The front of the torso and head or neck are involved; close-up view; non-clinician graders estimated 2 on the Monk skin tone scale; symptoms reported: itching; no relevant systemic symptoms; the subject is 50–59, female; the contributor notes the lesion is raised or bumpy; self-categorized by the patient as a rash; present for about one day — 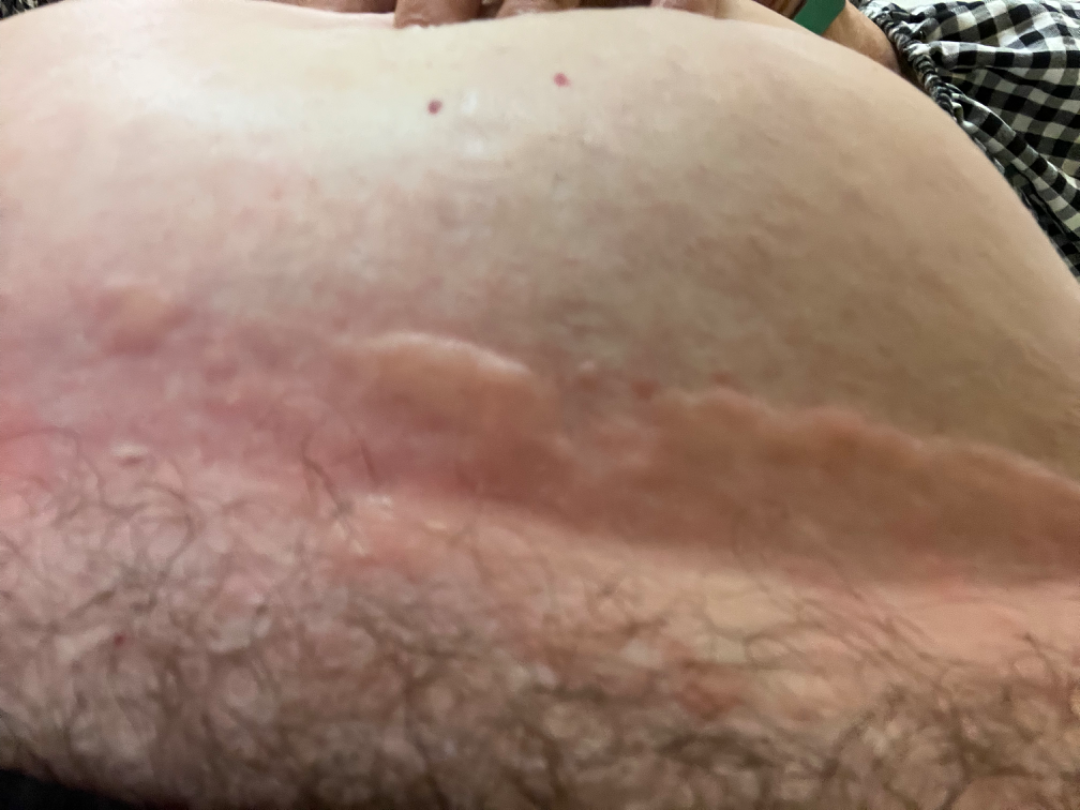differential:
  Urticaria: 1.0